A dermatoscopic image of a skin lesion.
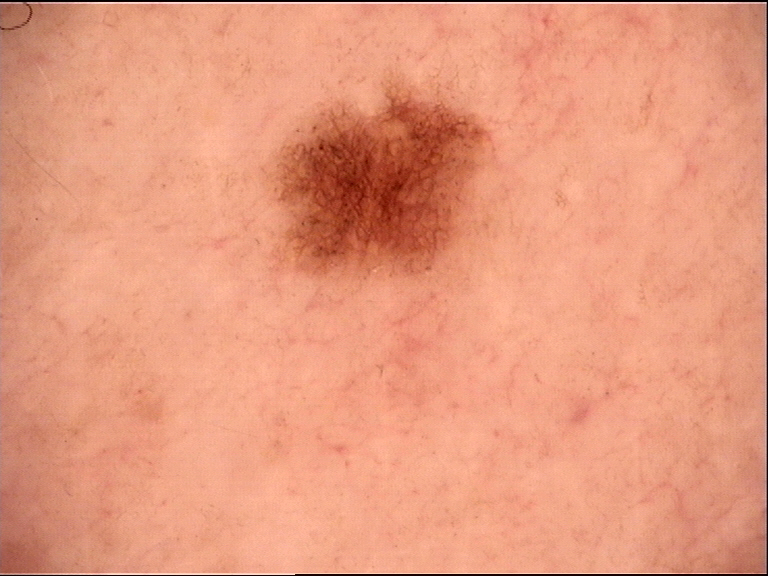diagnostic label = dysplastic junctional nevus (expert consensus).